A dermatoscopic image of a skin lesion; a female patient, aged 38-42 — 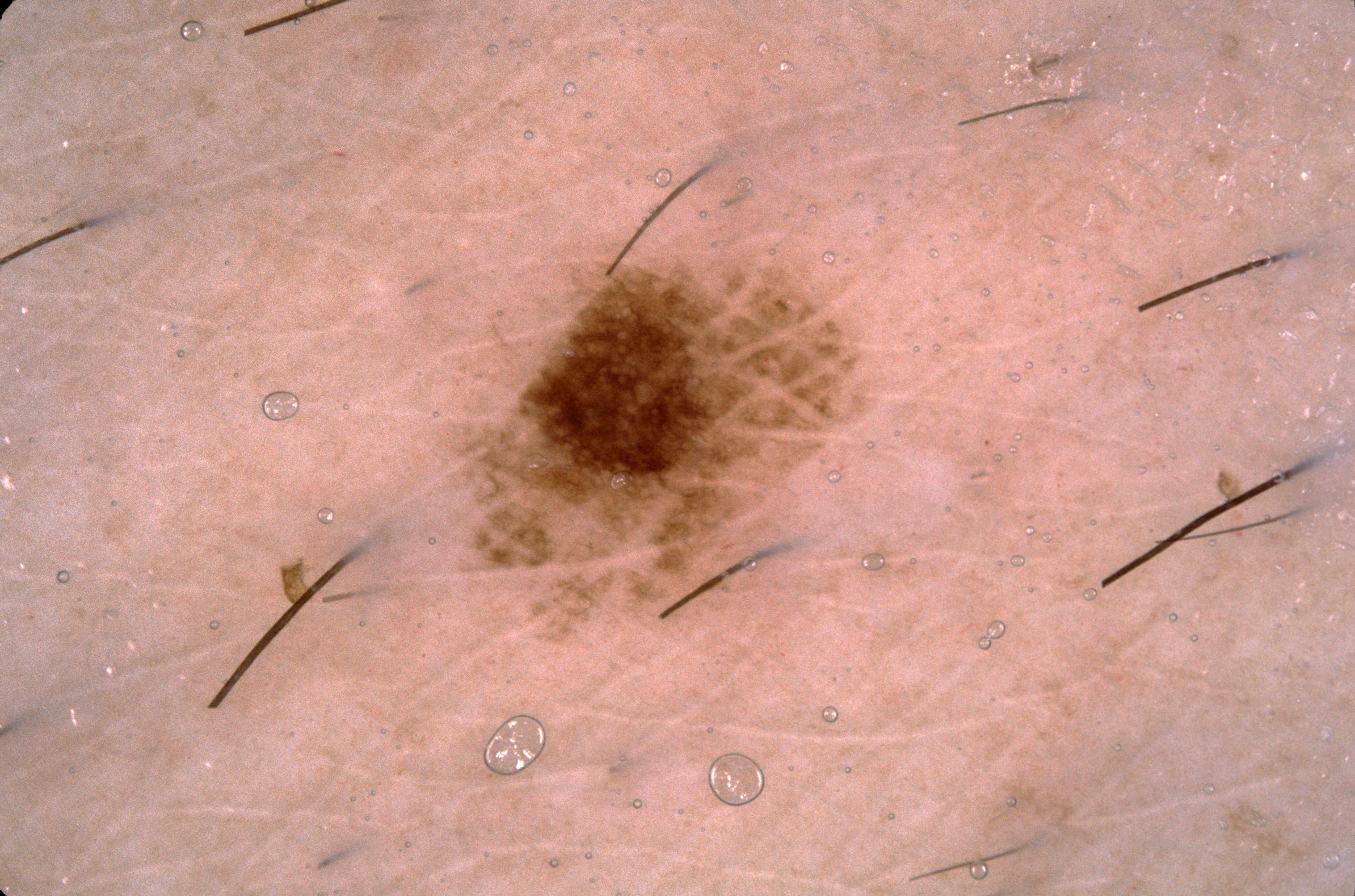Image and clinical context: The lesion occupies roughly 8% of the field. Dermoscopic assessment notes pigment network. As (left, top, right, bottom), the lesion's extent is bbox=[449, 163, 860, 635]. Conclusion: The clinical diagnosis was a melanocytic nevus, a benign skin lesion.